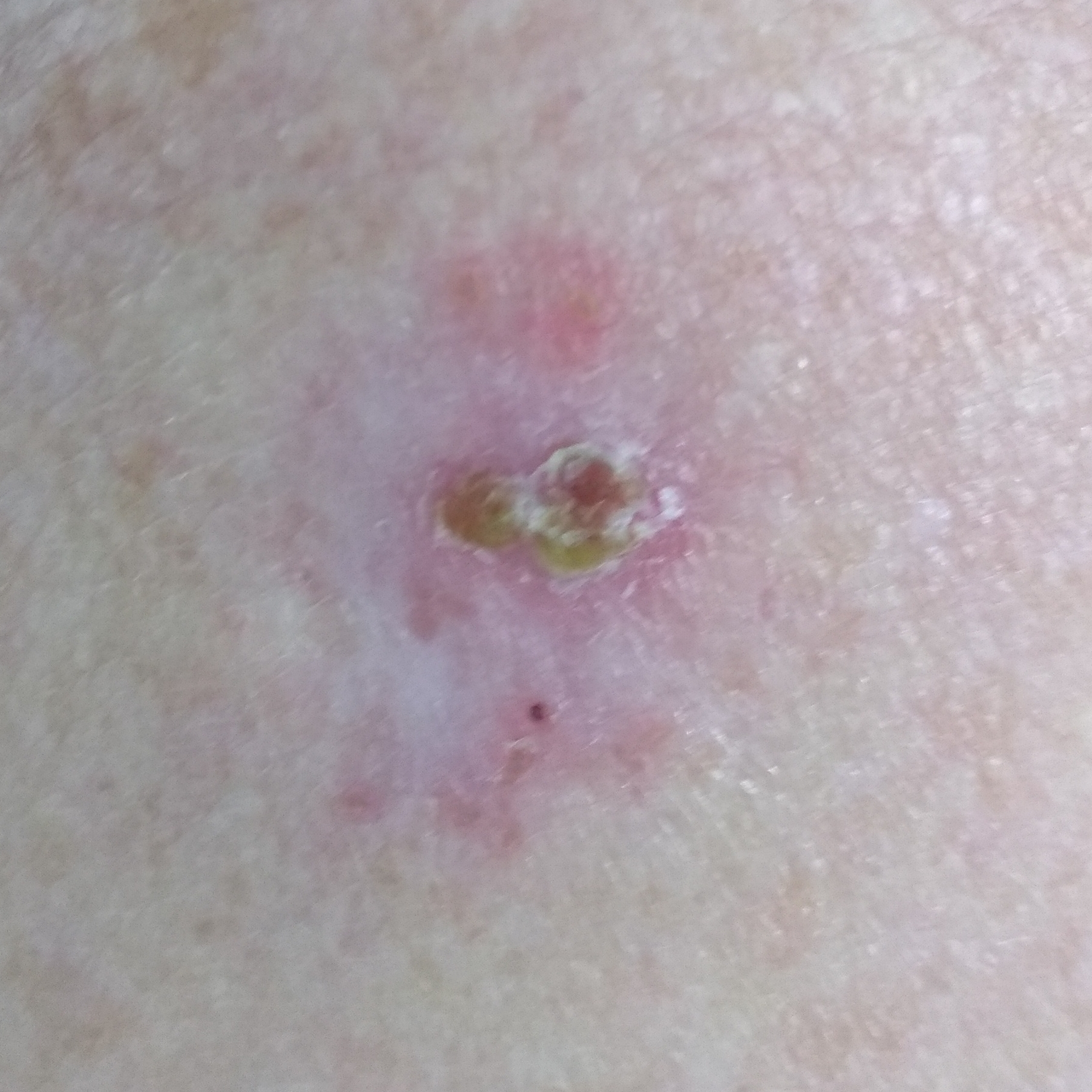<lesion>
  <risk_factors>
    <positive>prior cancer (patient or family), alcohol use</positive>
  </risk_factors>
  <image>smartphone clinical photo</image>
  <patient>
    <age>77</age>
    <gender>male</gender>
  </patient>
  <lesion_location>the chest</lesion_location>
  <lesion_size>
    <diameter_1_mm>19.0</diameter_1_mm>
    <diameter_2_mm>13.0</diameter_2_mm>
  </lesion_size>
  <symptoms>
    <present>bleeding, itching, pain</present>
    <absent>elevation</absent>
  </symptoms>
  <diagnosis>
    <name>basal cell carcinoma</name>
    <code>BCC</code>
    <malignancy>malignant</malignancy>
    <confirmation>histopathology</confirmation>
  </diagnosis>
</lesion>